A dermatoscopic image of a skin lesion.
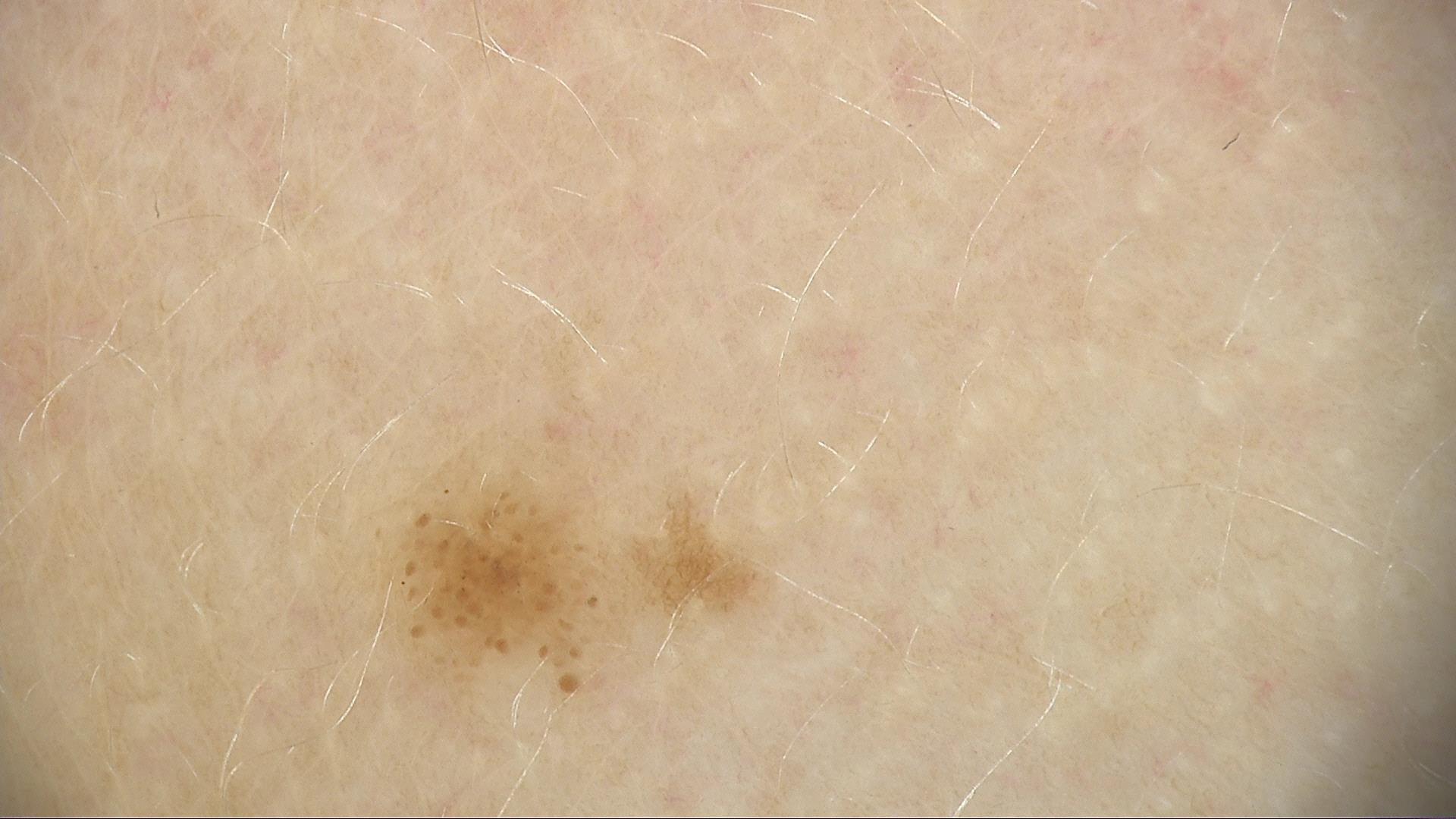diagnosis: dysplastic junctional nevus (expert consensus).